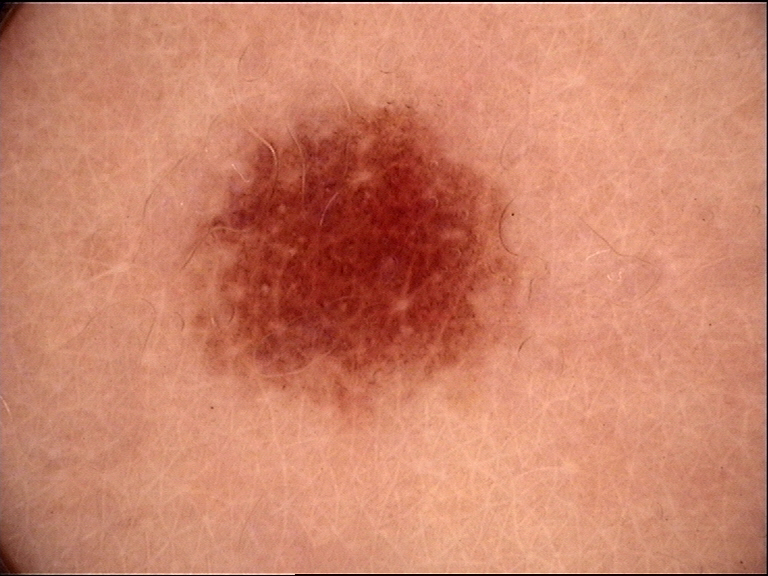assessment = dysplastic junctional nevus (expert consensus).